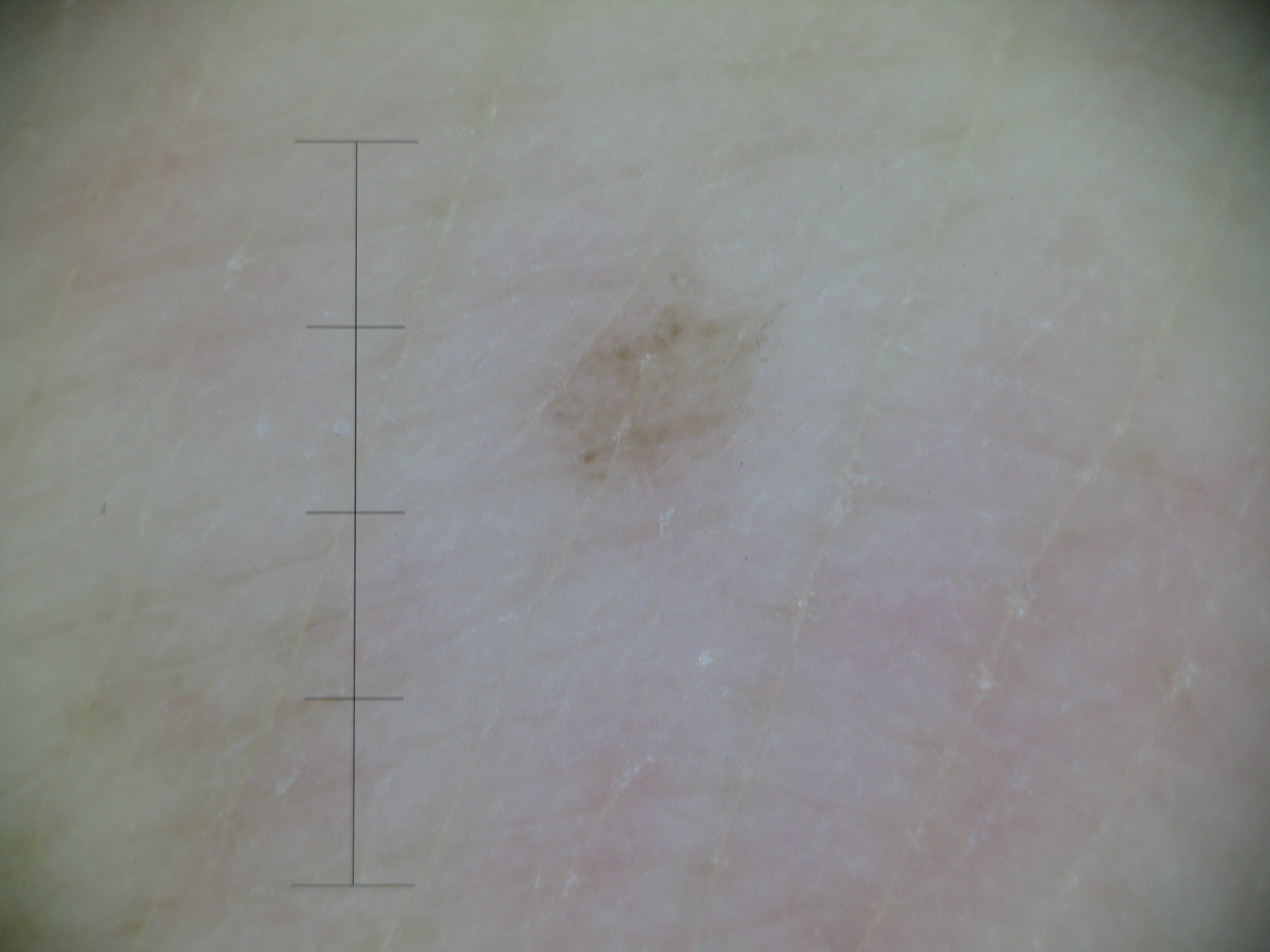Findings: A dermoscopy image of a single skin lesion. Impression: The diagnostic label was a banal lesion — an acral junctional nevus.